A dermoscopic close-up of a skin lesion.
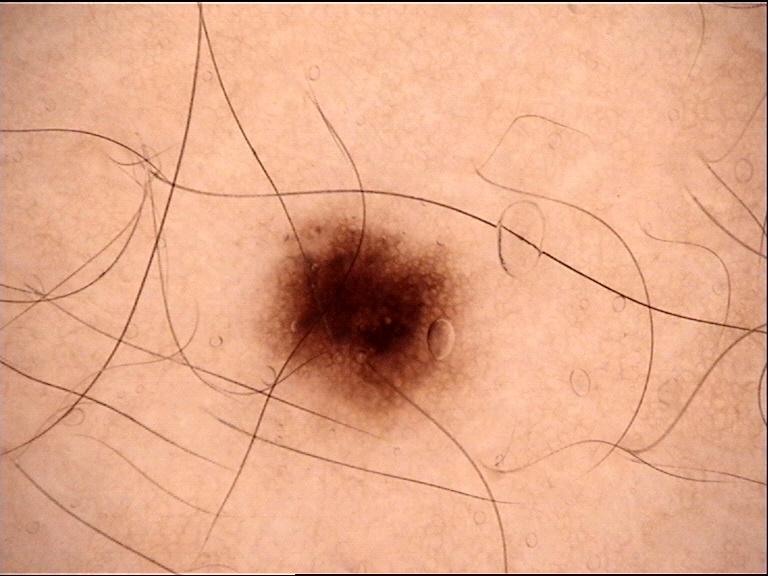lesion type: banal; class: junctional nevus (expert consensus).